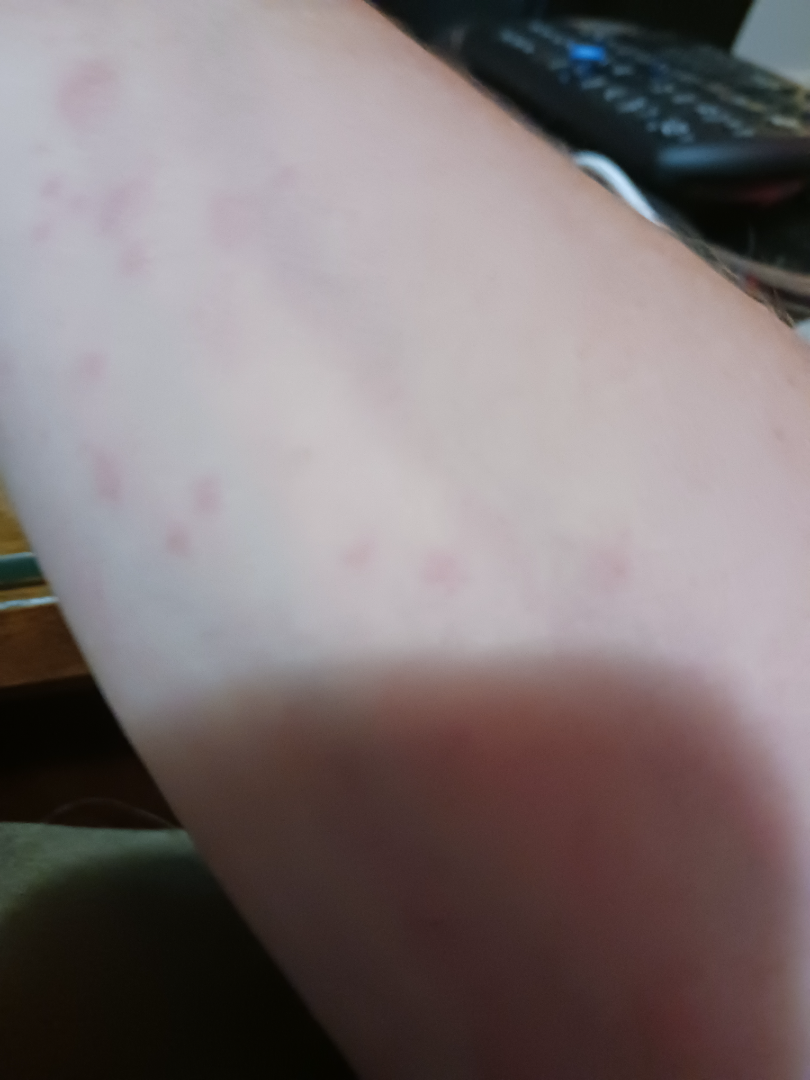{
  "assessment": "ungradable on photographic review",
  "shot_type": "close-up",
  "body_site": [
    "arm",
    "back of the hand"
  ],
  "symptoms": "itching",
  "patient": "female, age 50–59",
  "skin_tone": {
    "fitzpatrick": "II",
    "monk_skin_tone": 2
  }
}